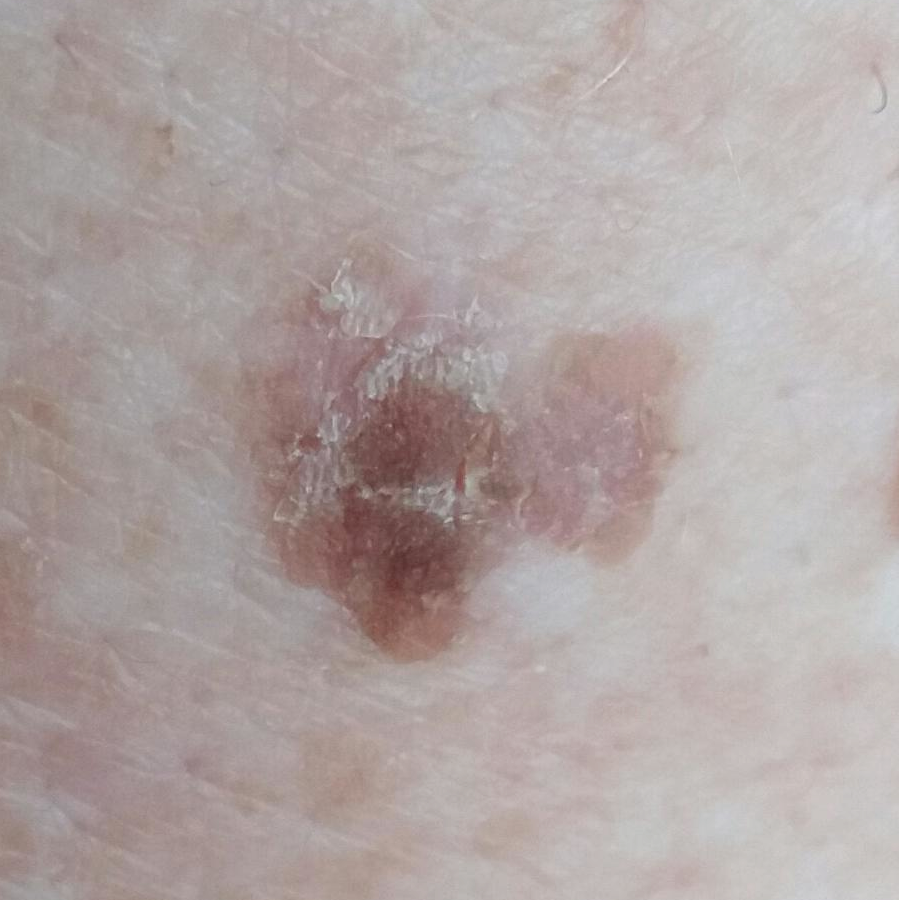Findings:
The lesion is located on the back. By the patient's account, the lesion is elevated, but does not itch and does not hurt.
Conclusion:
Clinically diagnosed as a seborrheic keratosis.